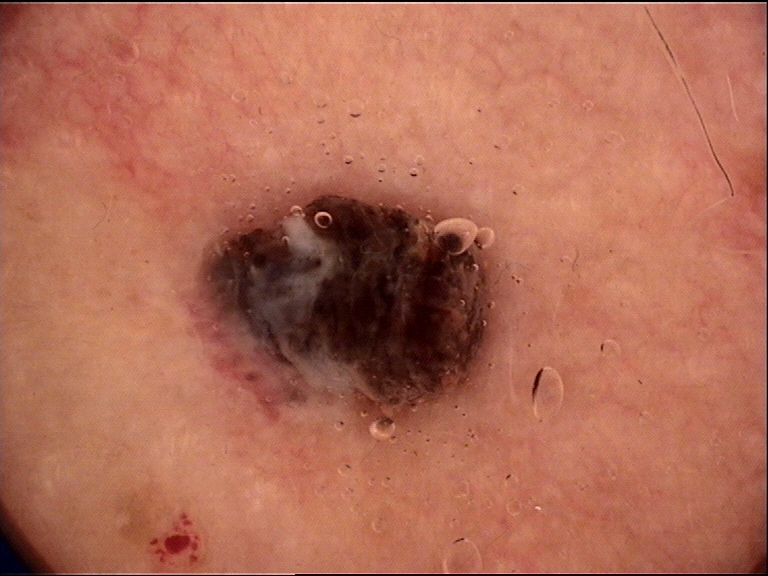Biopsy-confirmed as a melanoma.